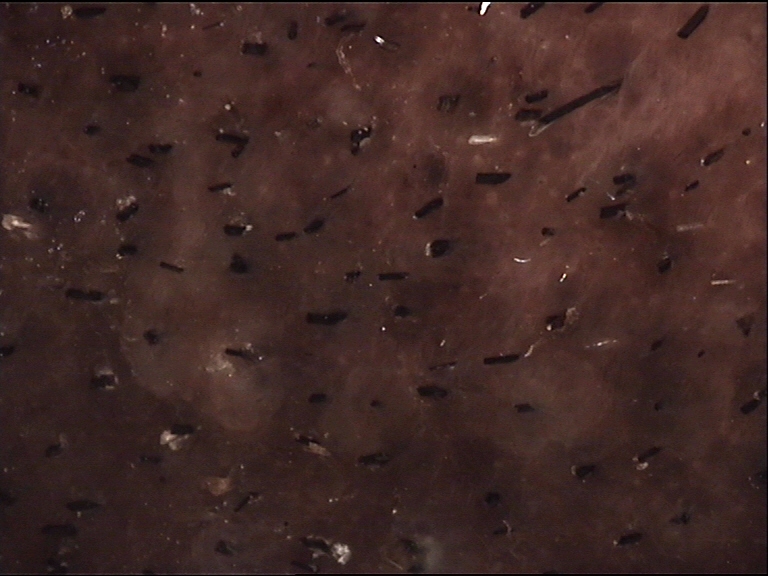A dermoscopic image of a skin lesion. This is a banal lesion. Diagnosed as a congenital compound nevus.